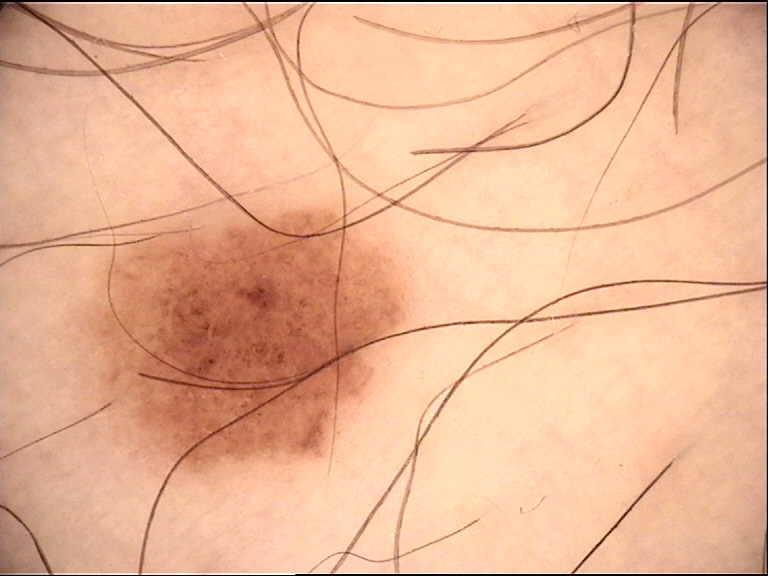The diagnostic label was a dysplastic junctional nevus.